The photograph was taken at a distance · the affected area is the arm · female subject, age 18–29 — 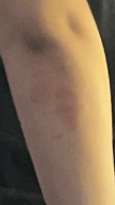{
  "assessment": "ungradable on photographic review"
}